A skin lesion imaged with a dermatoscope. A male subject, aged around 50.
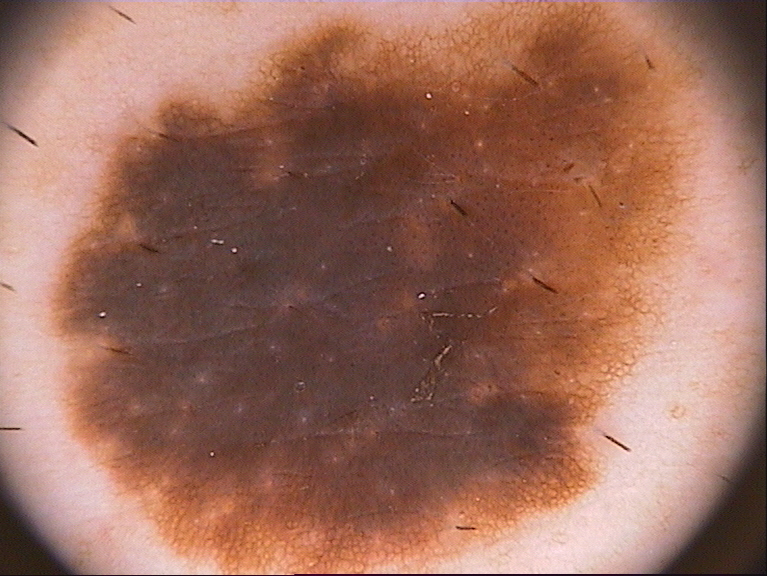| field | value |
|---|---|
| bounding box | [46,1,712,570] |
| lesion extent | ~68% of the field |
| dermoscopic features | pigment network and globules; absent: milia-like cysts, streaks, and negative network |
| diagnosis | a melanocytic nevus, a benign skin lesion |